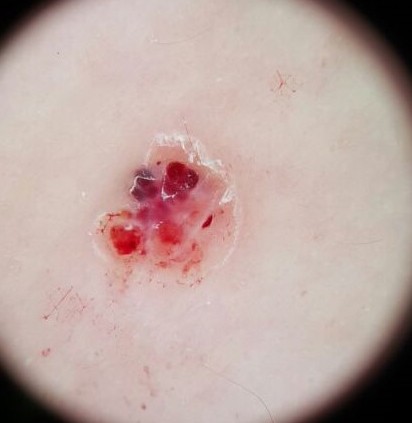A dermoscopic close-up of a skin lesion. This is a vascular lesion. Consistent with an angiokeratoma.